The lesion involves the arm, a close-up photograph — 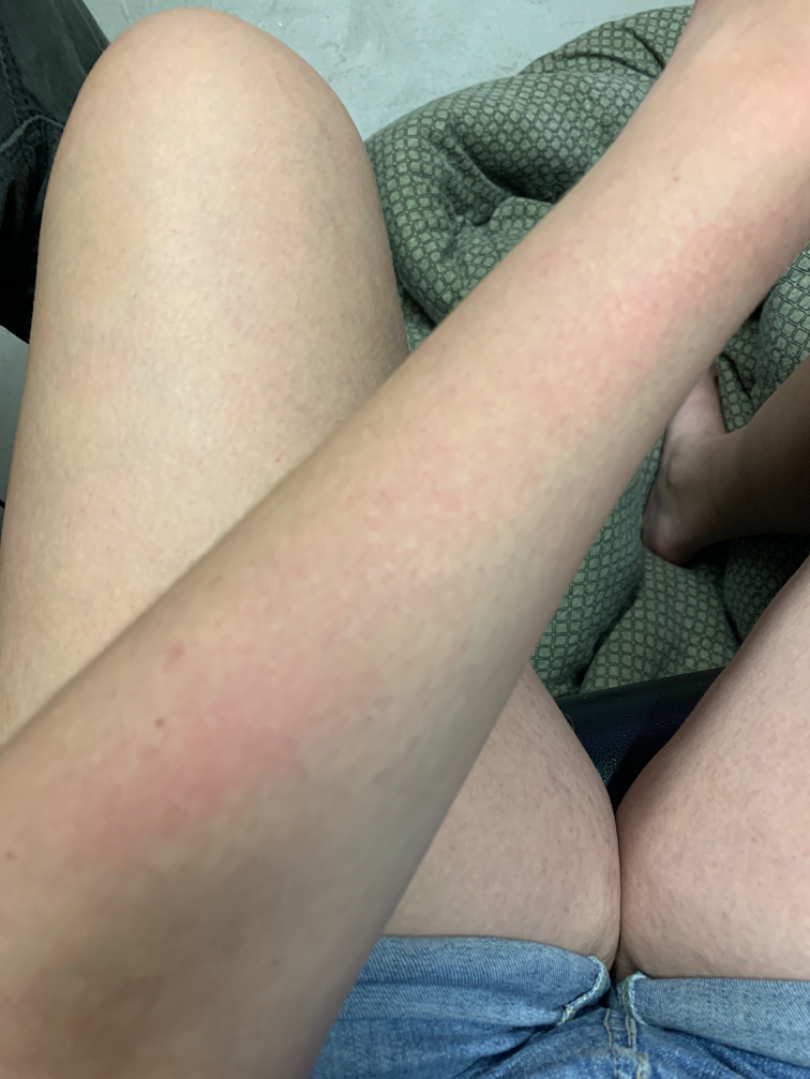assessment — indeterminate from the photograph.